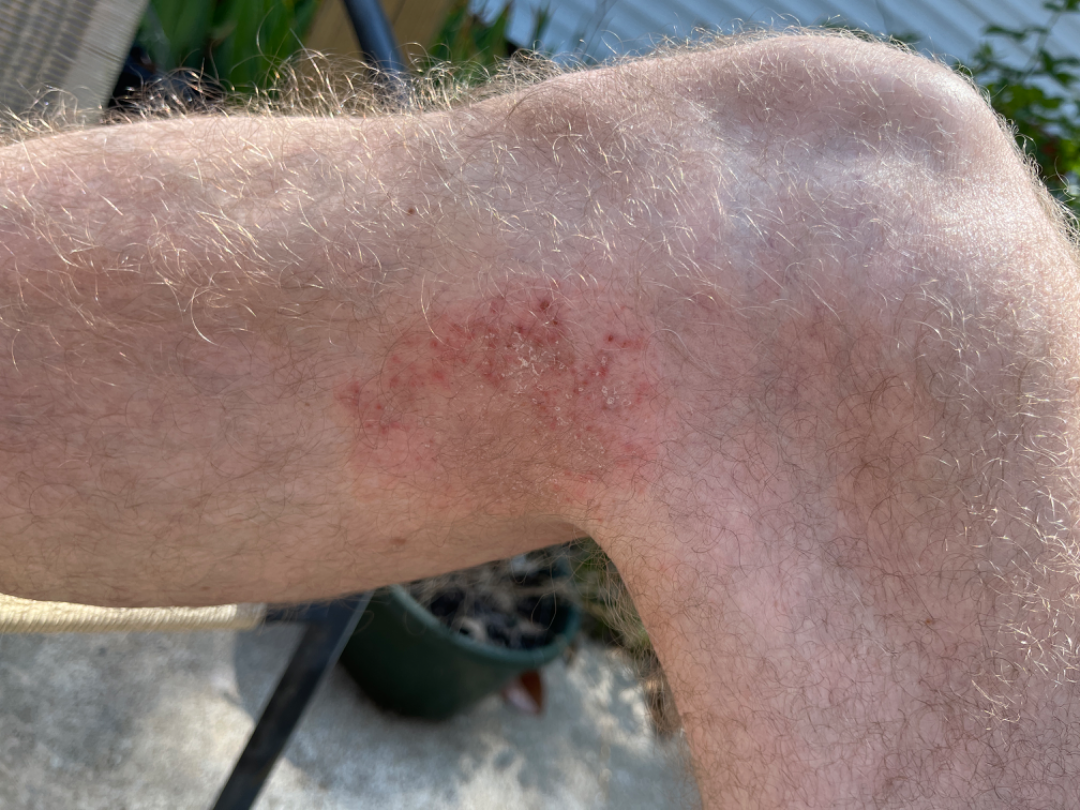{"patient_category": "a growth or mole", "shot_type": "close-up", "symptoms": "itching", "patient": "male, age 50–59", "duration": "one to four weeks", "body_site": "leg", "texture": ["fluid-filled", "raised or bumpy"], "differential": {"tied_lead": ["Tinea", "Psoriasis", "Eczema"]}}